An image taken at a distance · the patient also reports fatigue and chills · texture is reported as flat and rough or flaky · the patient reports the condition has been present for one to four weeks: 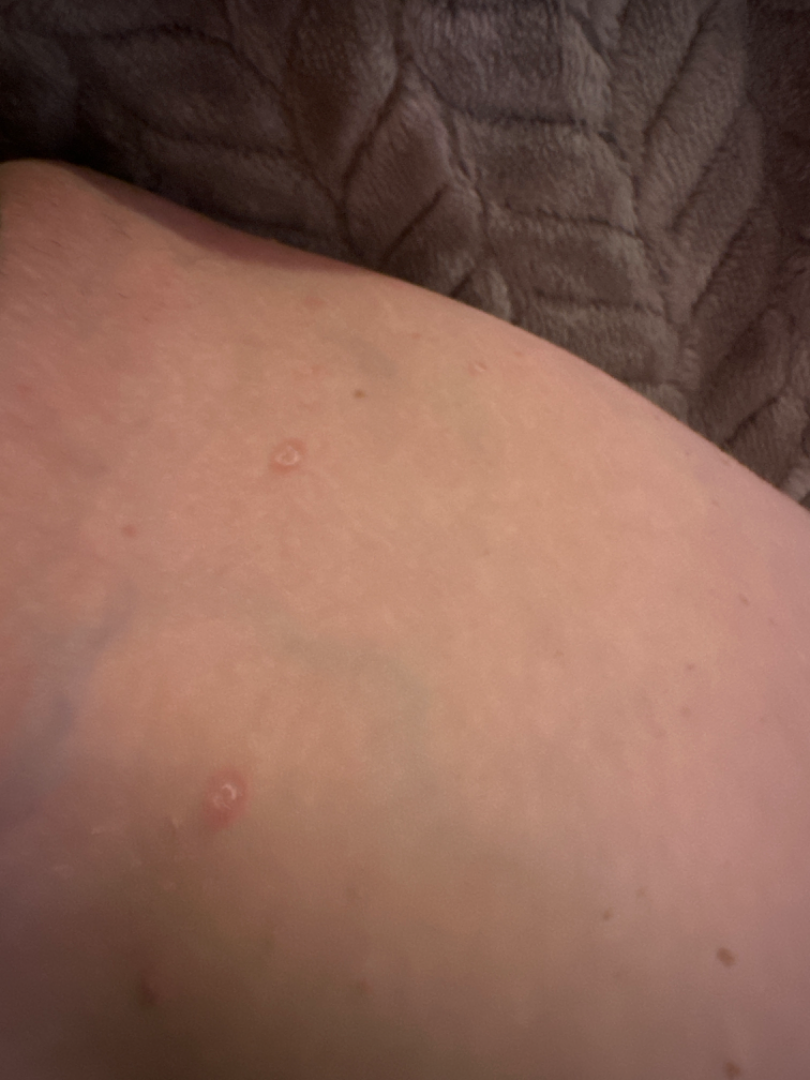Q: What conditions are considered?
A: most consistent with Pityriasis rosea; possibly Psoriasis